A clinical photograph showing a skin lesion; a patient age 87: 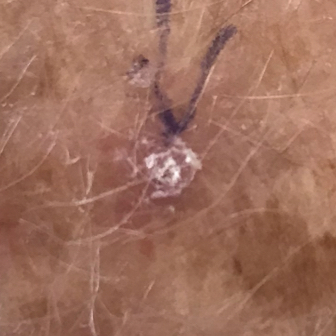| key | value |
|---|---|
| anatomic site | a forearm |
| symptoms | itching |
| assessment | actinic keratosis (clinical consensus) |